The photo was captured at an angle:
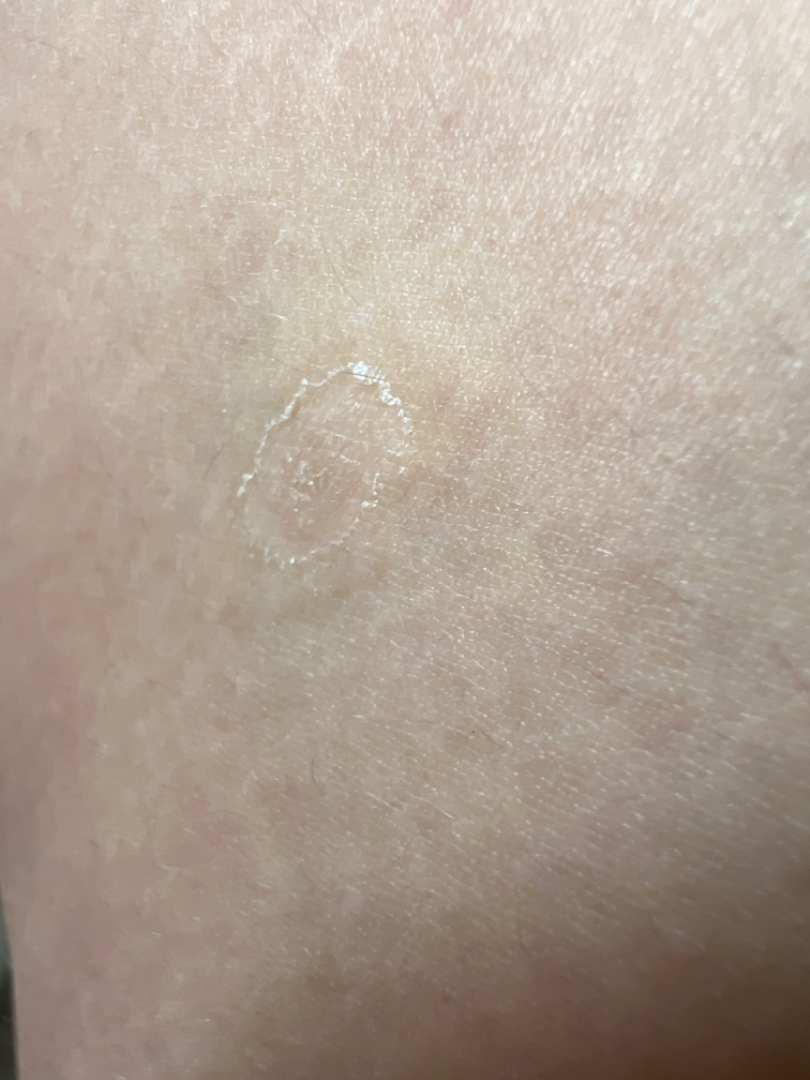On dermatologist assessment of the image: Porokeratosis, Xerosis and Keratosis were considered with similar weight.